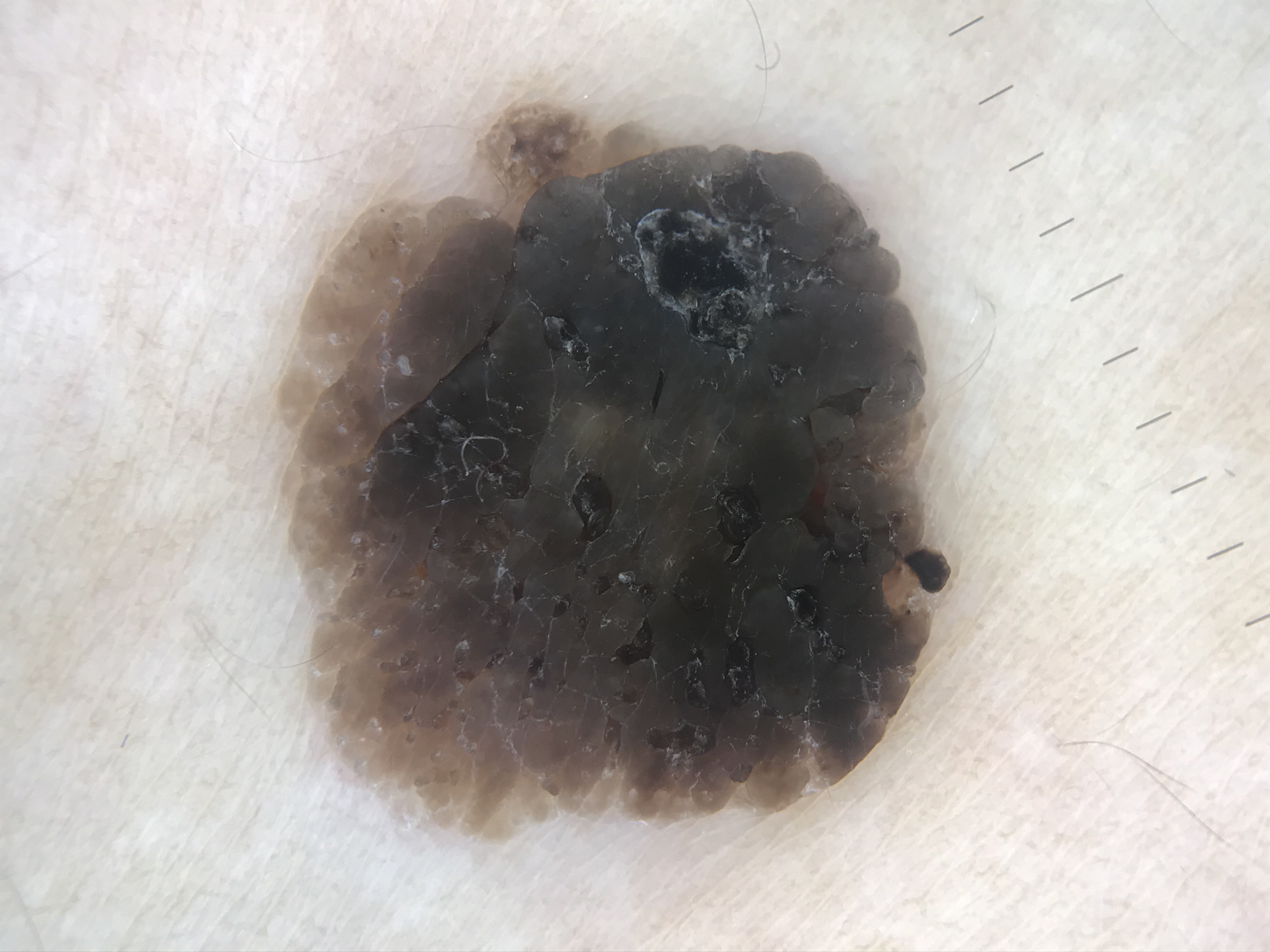Q: What is the imaging modality?
A: dermatoscopy
Q: What is this lesion?
A: seborrheic keratosis (expert consensus)